No relevant systemic symptoms; the leg is involved; close-up view; symptoms reported: bothersome appearance; the patient considered this a rash; the condition has been present for one to four weeks; female subject, age 60–69: 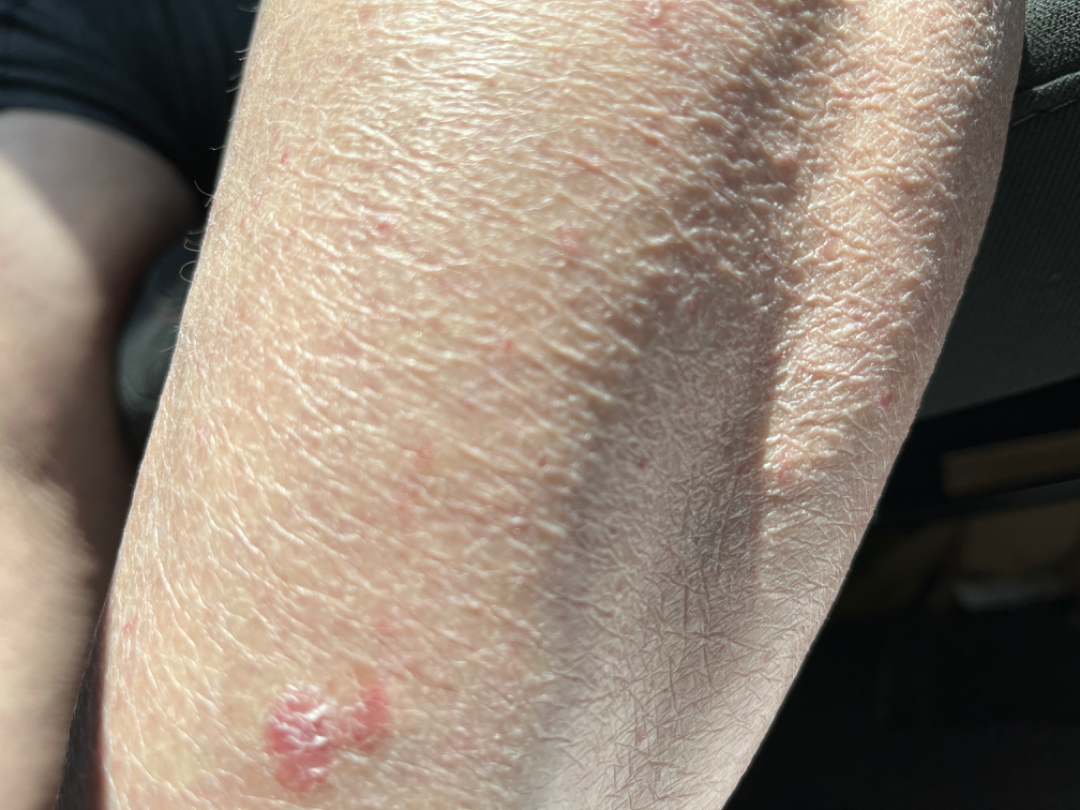Findings:
* assessment — indeterminate